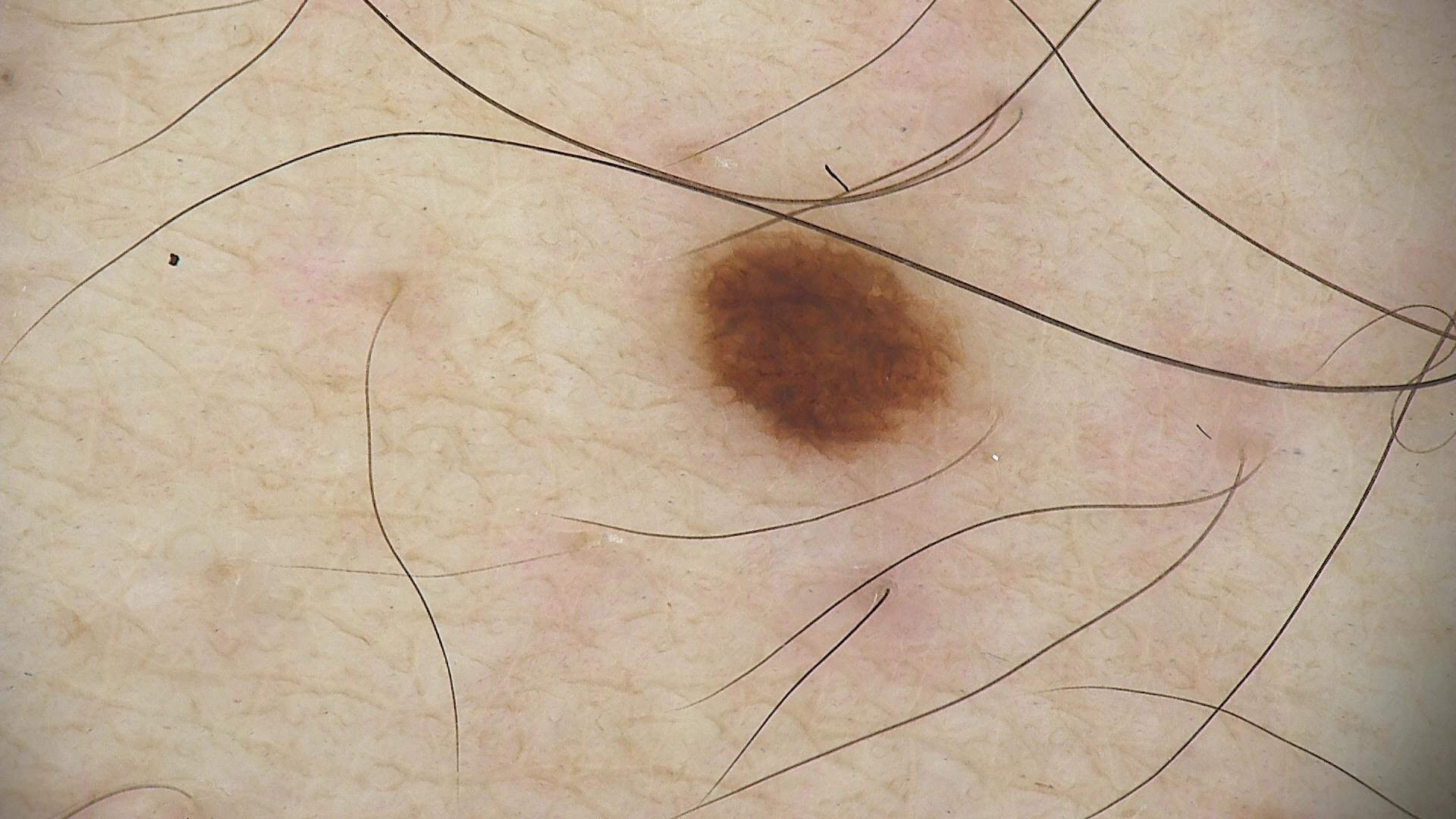Findings: A skin lesion imaged with a dermatoscope. Conclusion: Consistent with a dysplastic junctional nevus.